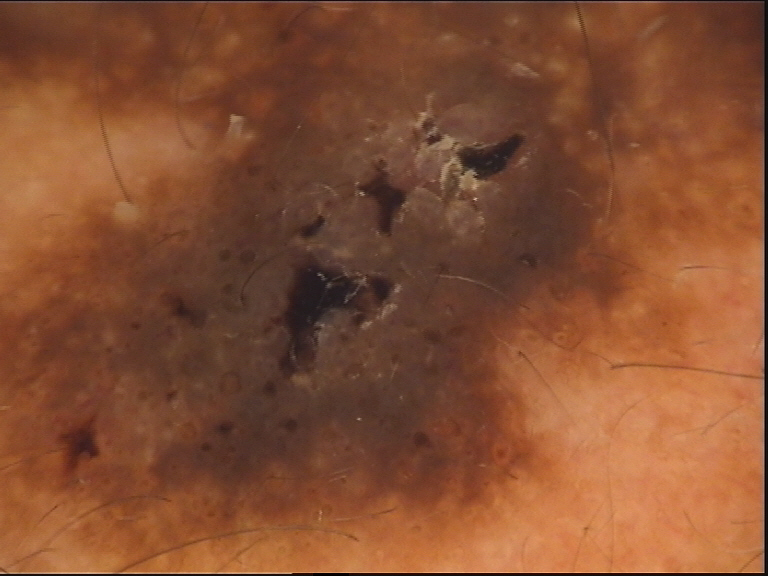image — dermoscopy | diagnosis — seborrheic keratosis (expert consensus).